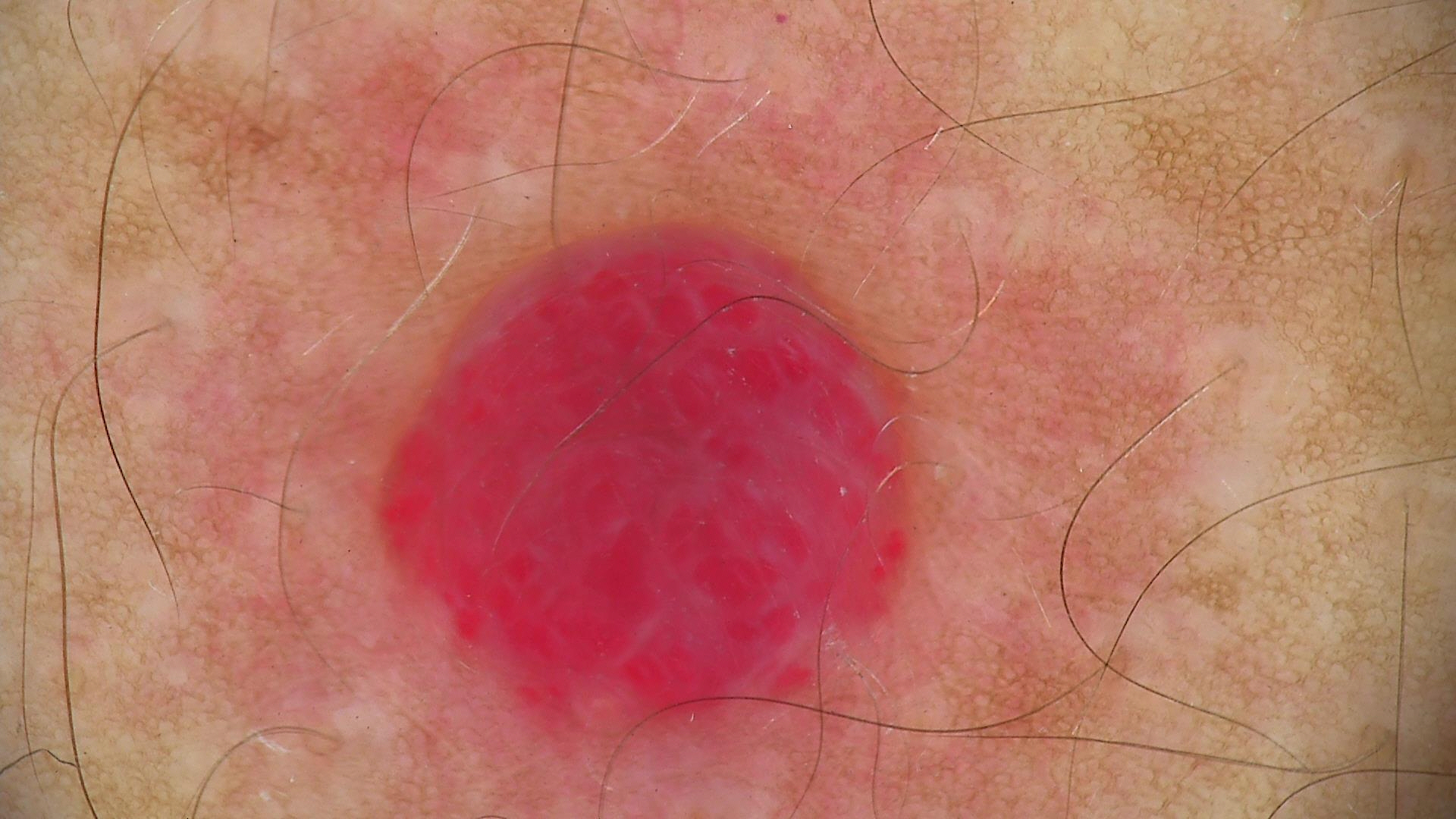imaging = dermatoscopy
class = hemangioma (expert consensus)